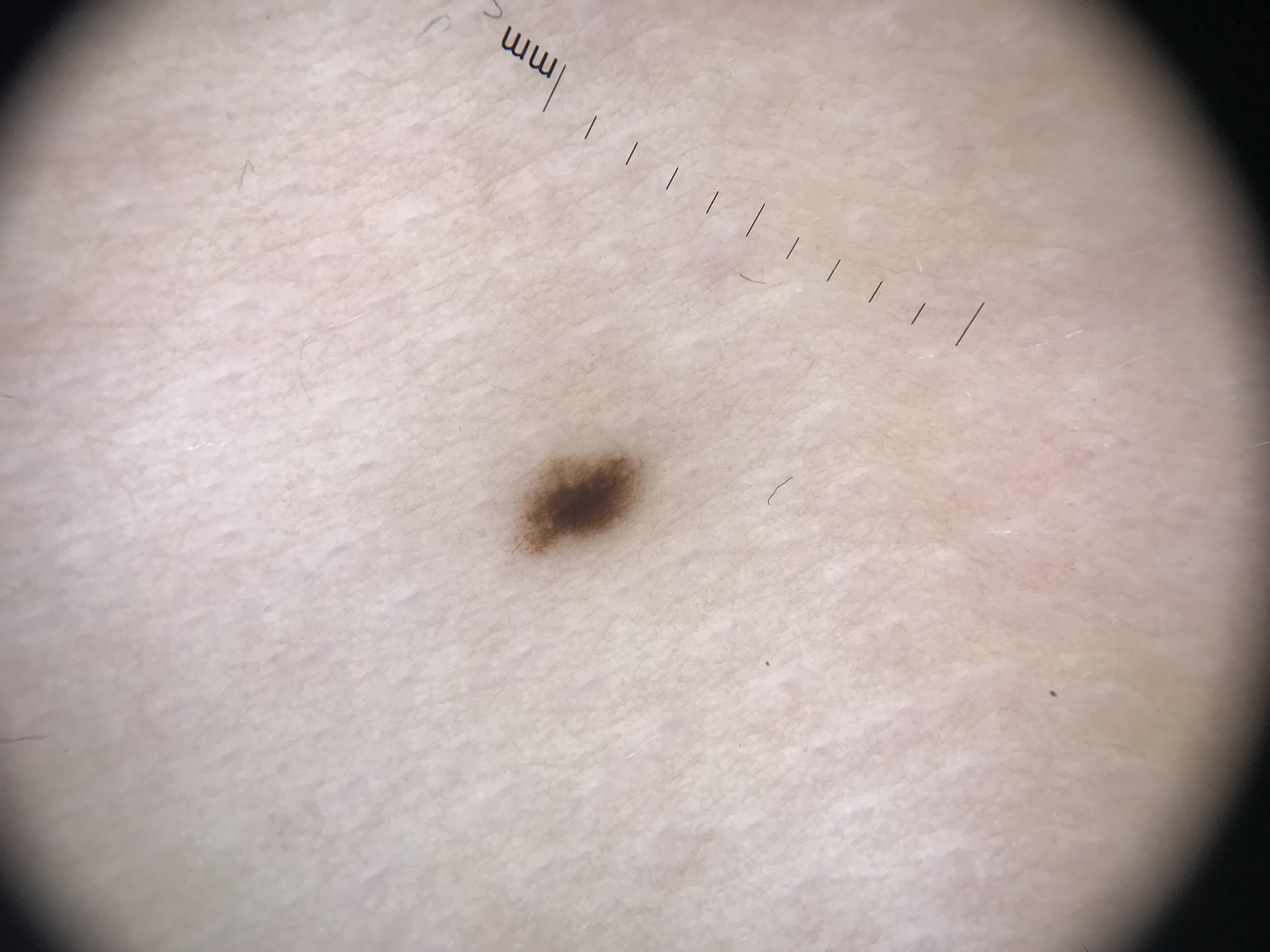modality — dermatoscopy | classification — banal | diagnostic label — junctional nevus (expert consensus).